Located on the leg. The subject is a female aged 18–29. Present for one to four weeks. This is a close-up image:
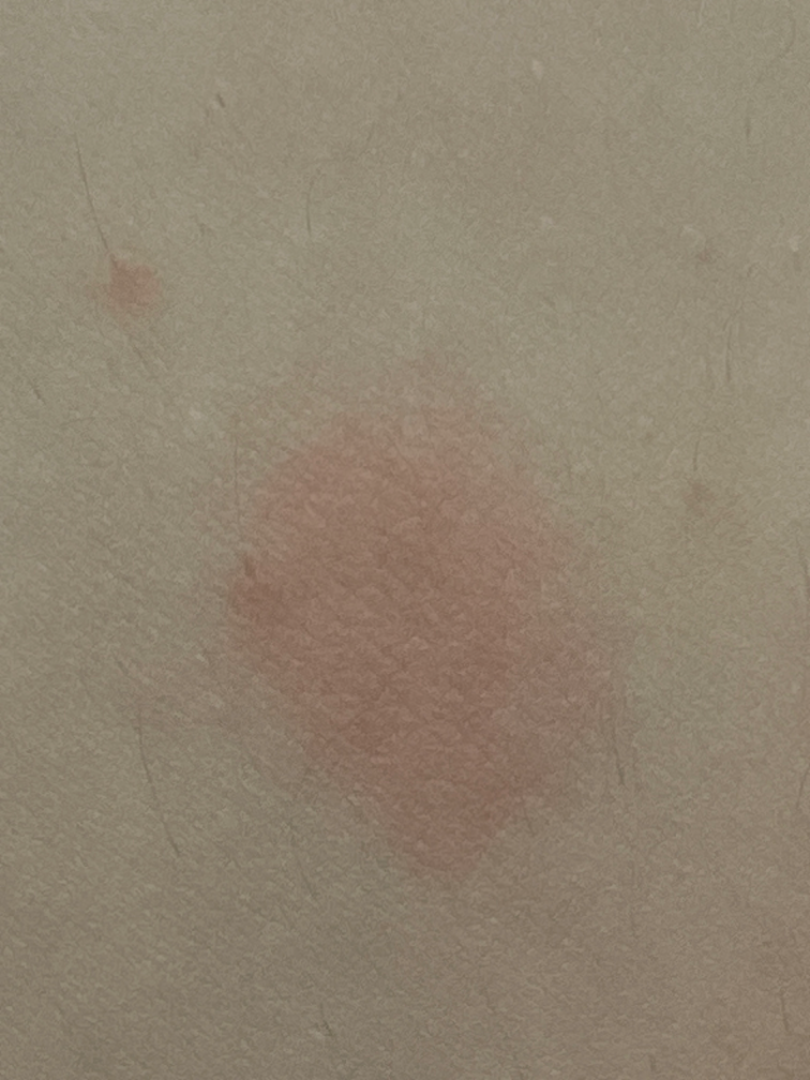Assessment:
The reviewing clinician's impression was: Sweet syndrome, Insect Bite and Eczema were each considered, in no particular order.